Acquired for a research image collection, with no referral diagnosis; the patient says their skin tans without first burning; few moles overall by the patient's own estimate; a female subject 68 years of age — 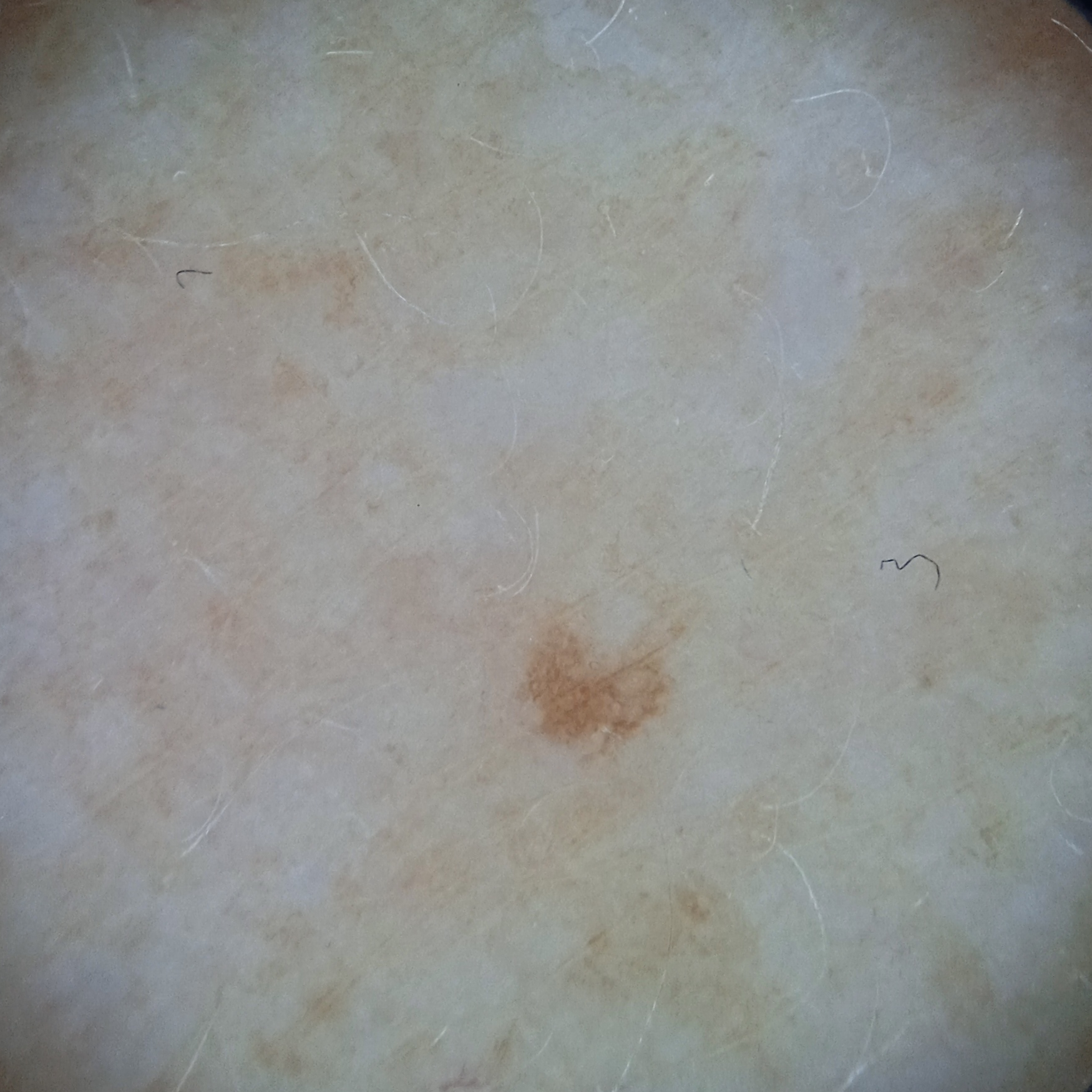Findings:
* site: an arm
* size: 1.7 mm
* diagnosis: melanocytic nevus (dermatologist consensus)